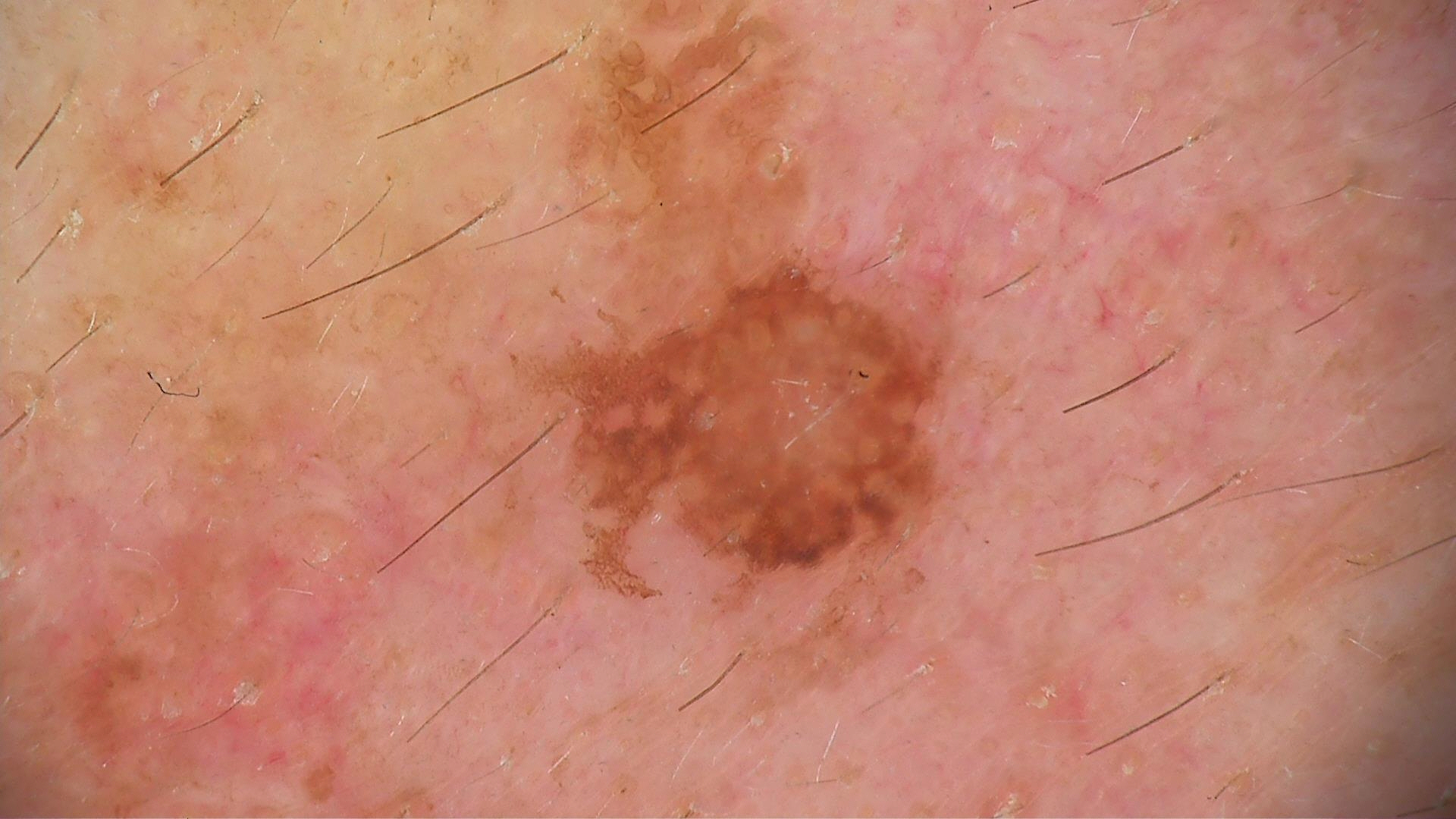* label · seborrheic keratosis (expert consensus)